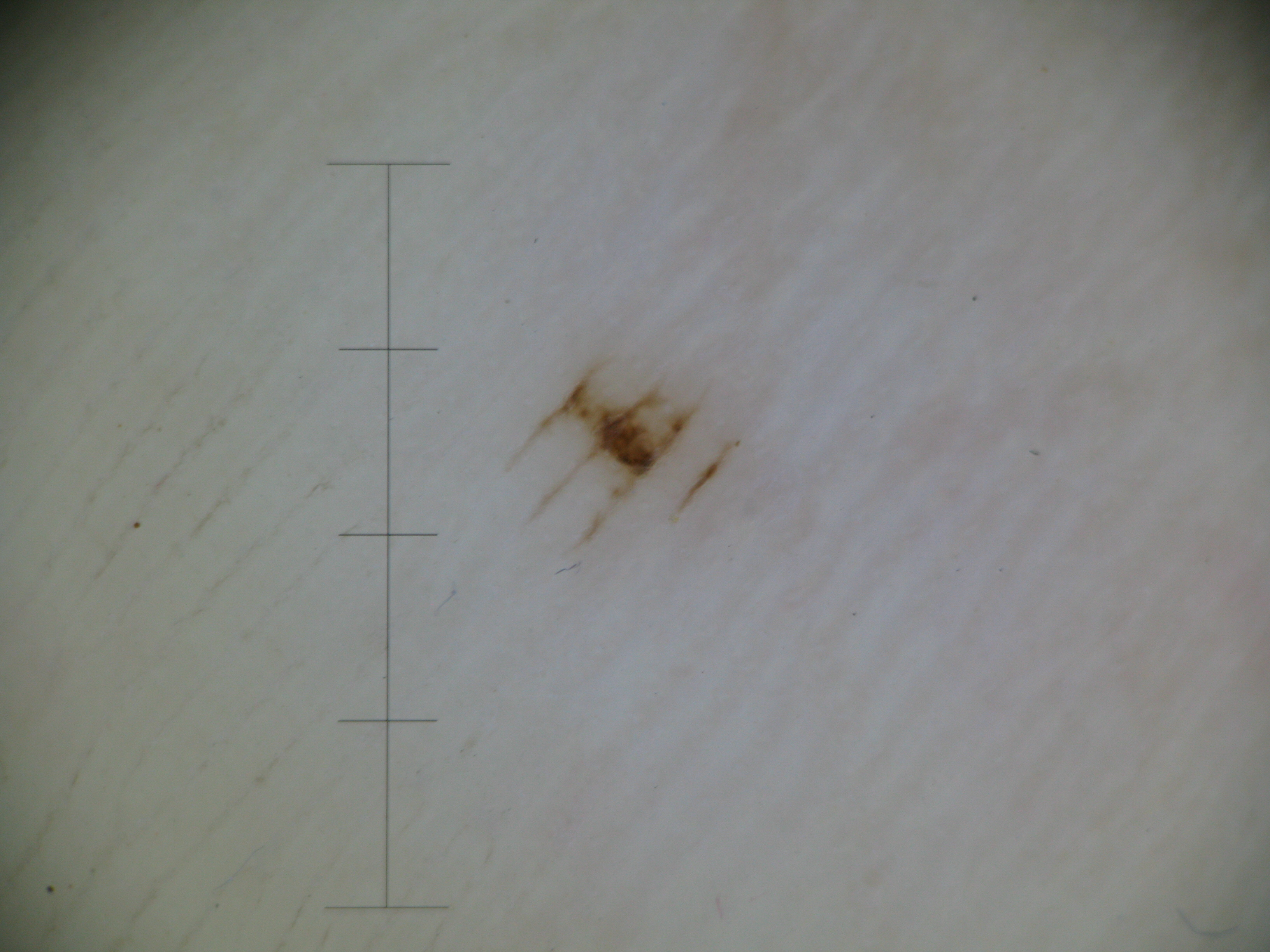Q: What is this lesion?
A: acral junctional nevus (expert consensus)